The lesion involves the arm; the photograph is a close-up of the affected area; the patient is 18–29, female:
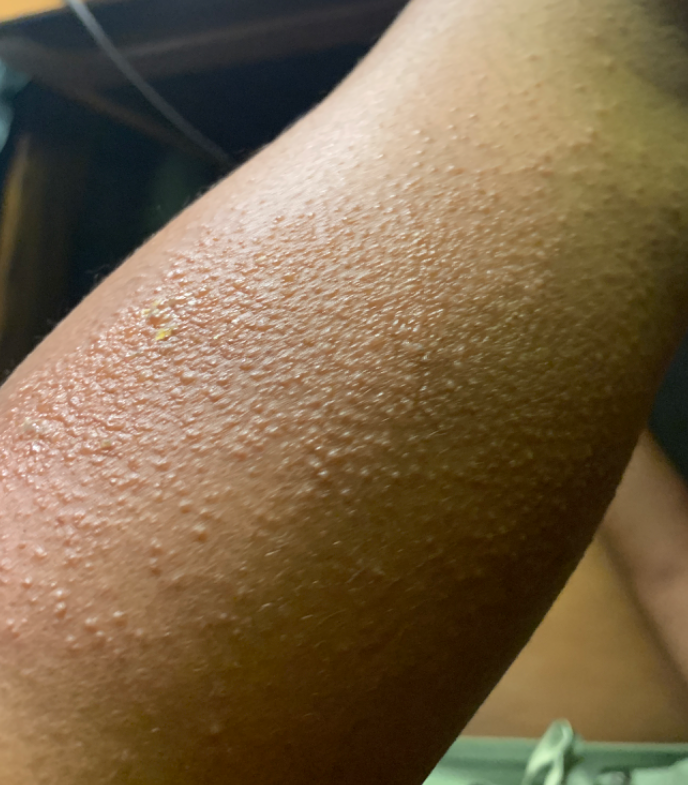{
  "skin_tone": {
    "fitzpatrick": "V",
    "monk_skin_tone": [
      3,
      4
    ]
  },
  "duration": "less than one week",
  "patient_category": "a rash",
  "differential": "Allergic Contact Dermatitis"
}